The patient indicates the condition has been present for less than one week. The leg is involved. No constitutional symptoms were reported. Skin tone: Fitzpatrick II; lay reviewers estimated Monk Skin Tone 2 or 4. The photo was captured at an angle. Texture is reported as flat — 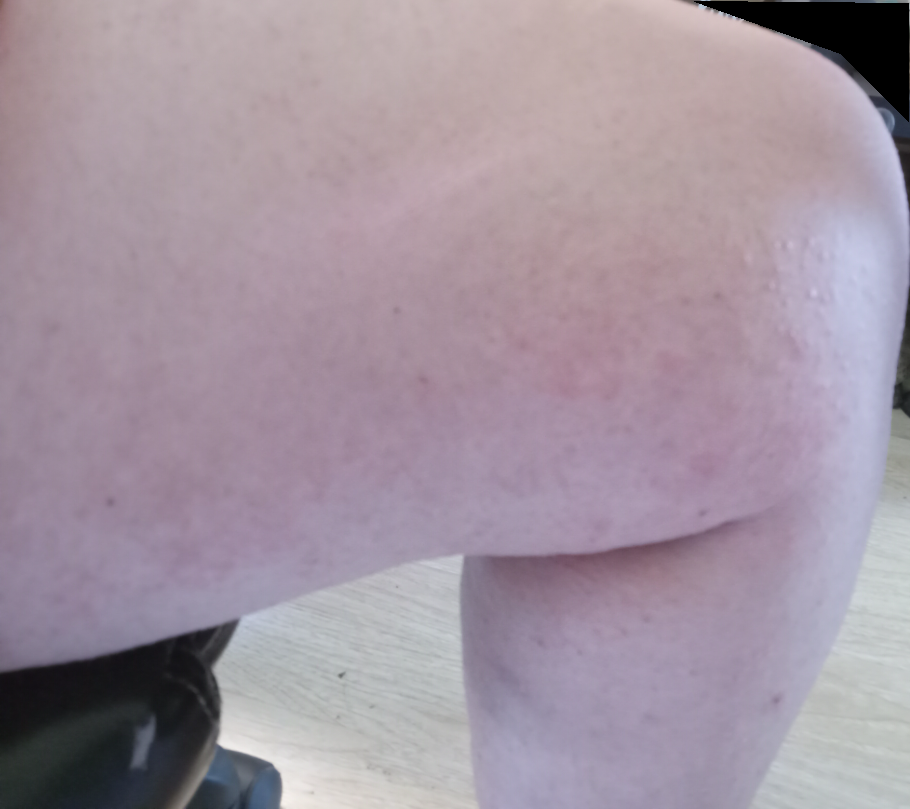No differential diagnosis could be assigned on photographic review.